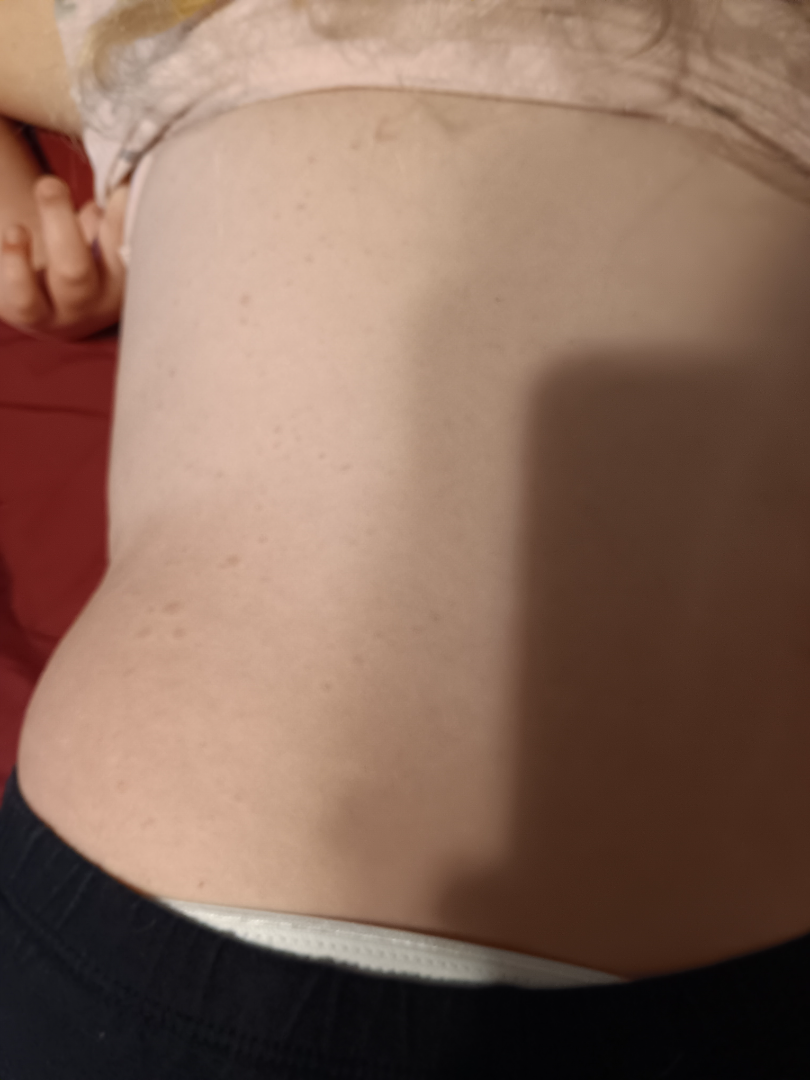Findings:
- assessment · ungradable on photographic review
- body site · back of the torso, top or side of the foot, front of the torso, back of the hand, head or neck, arm and leg
- photo taken · at an angle